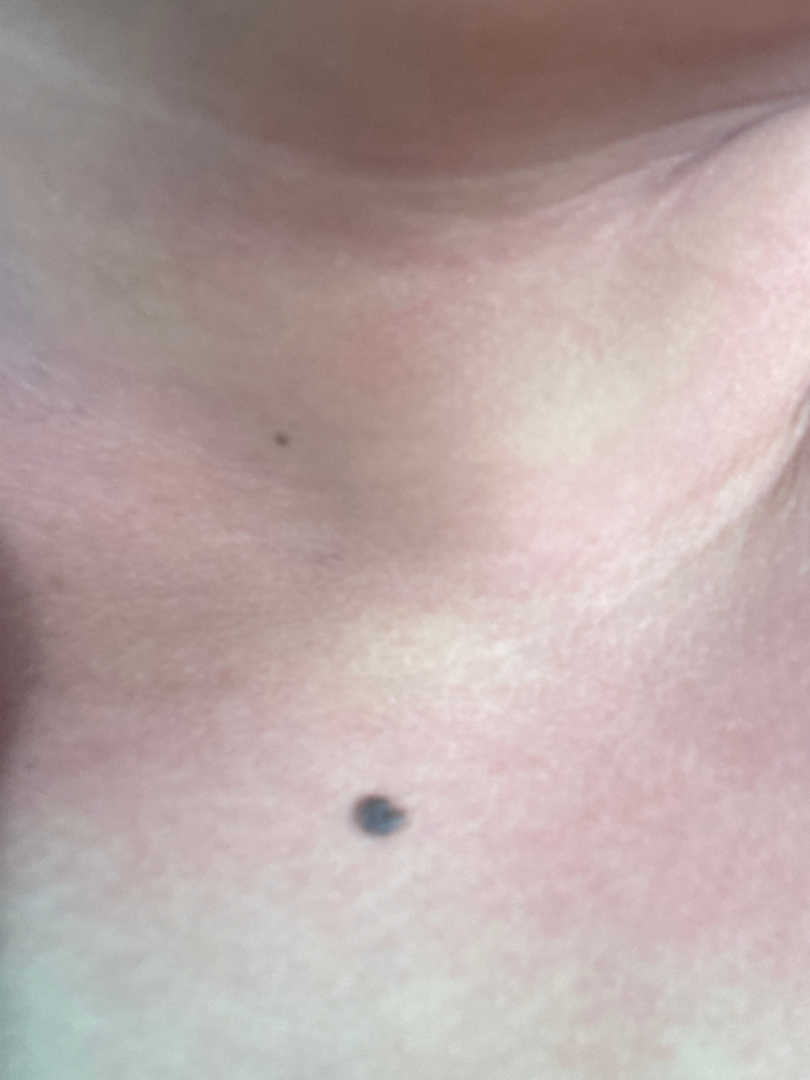The contributor is a female aged 30–39. The affected area is the palm, head or neck, leg, arm, back of the hand and sole of the foot. The patient notes itching, darkening and burning. Reported duration is more than five years. An image taken at an angle. On photographic review: Intertrigo (primary); Allergic Contact Dermatitis (considered); Irritant Contact Dermatitis (lower probability); Photodermatitis (lower probability); Cellulitis (lower probability); Hypersensitivity (lower probability).